A dermoscopic close-up of a skin lesion: 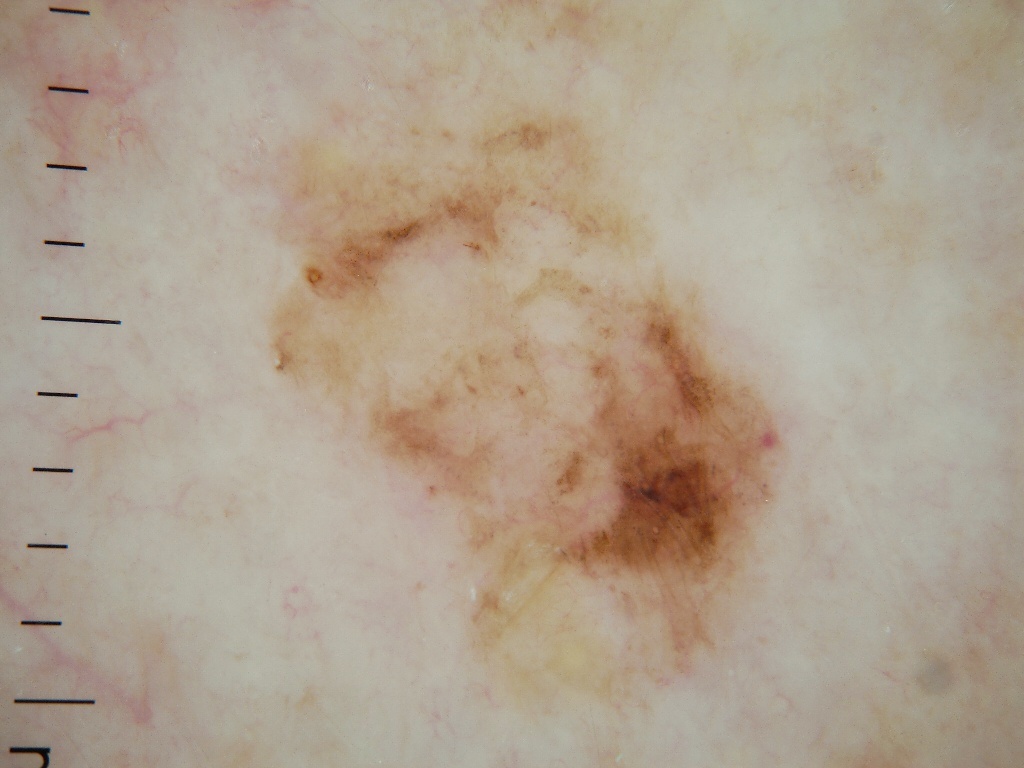As (left, top, right, bottom), the visible lesion spans (242, 2, 796, 762). The lesion covers approximately 37% of the dermoscopic field. Confirmed on histopathology as a skin cancer.